A dermoscopy image of a single skin lesion: 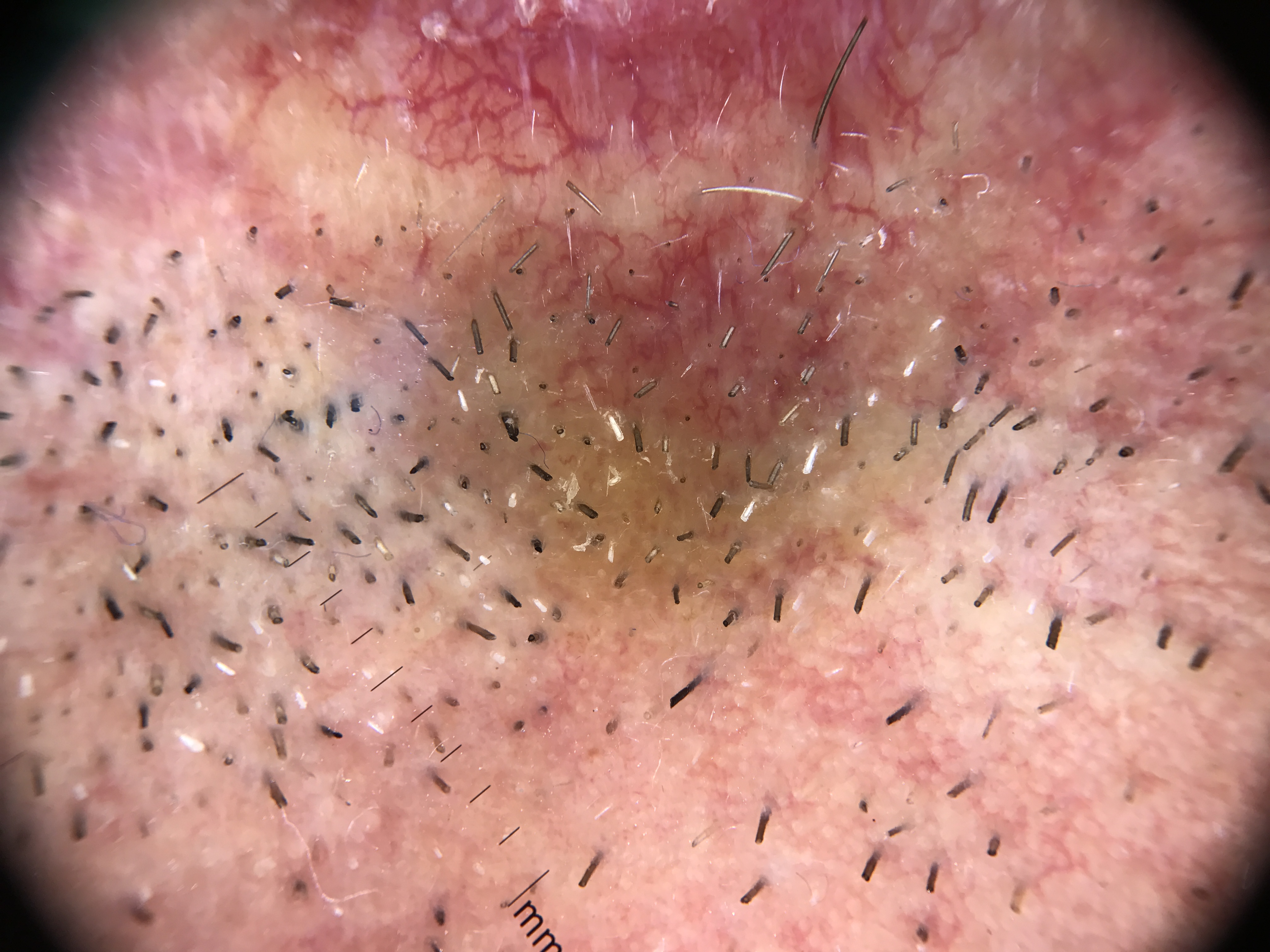{
  "diagnosis": {
    "name": "basal cell carcinoma",
    "code": "bcc",
    "malignancy": "malignant",
    "super_class": "non-melanocytic",
    "confirmation": "histopathology"
  }
}